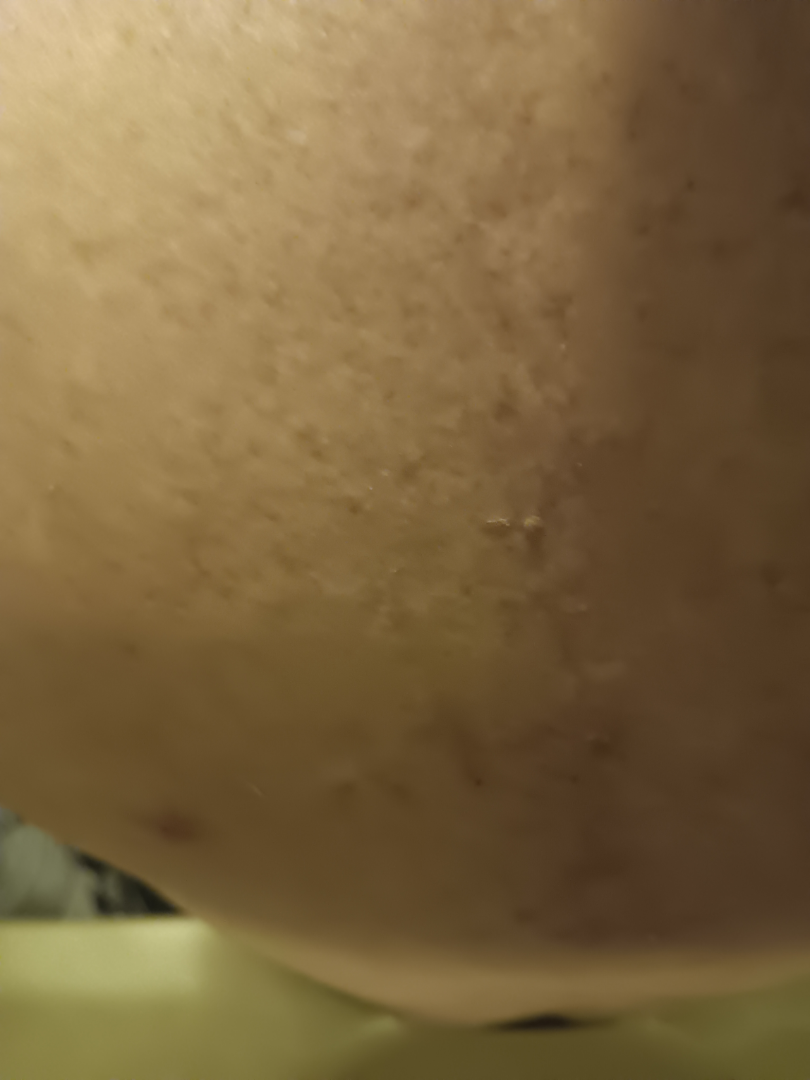Patient information:
Texture is reported as raised or bumpy. The photo was captured at an angle. The contributor is a male aged 50–59. The affected area is the back of the torso.